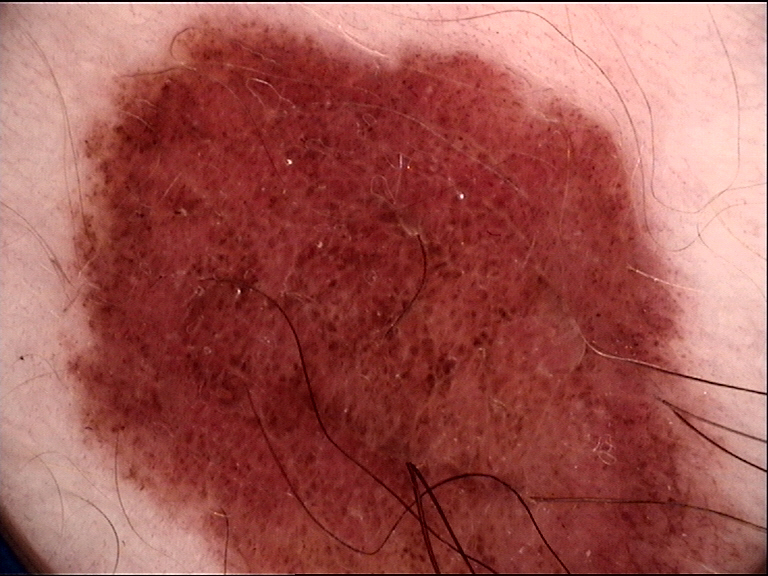Classified as a congenital compound nevus.